A subject 70 years old: 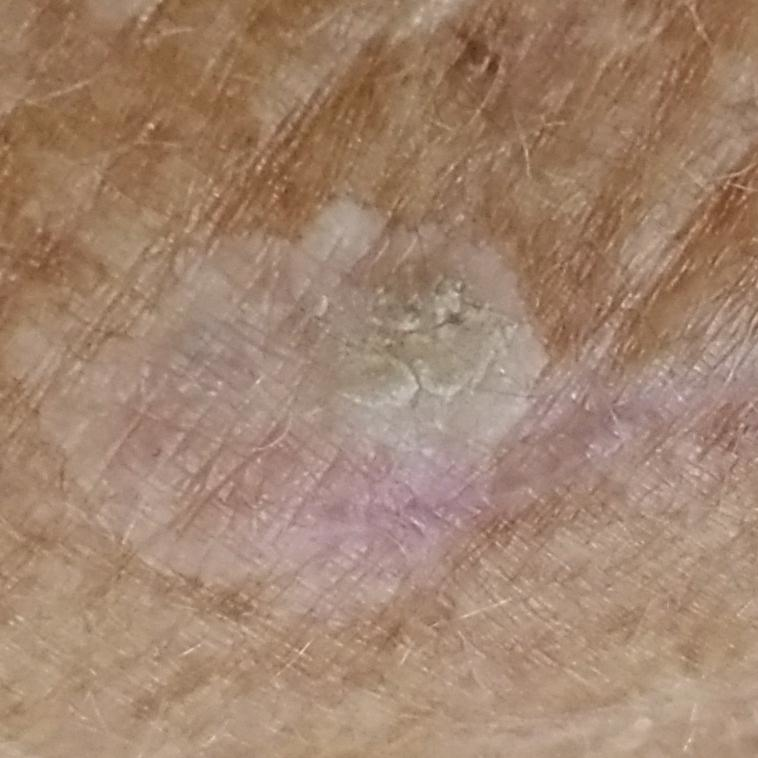| field | value |
|---|---|
| diagnostic label | actinic keratosis (clinical consensus) |